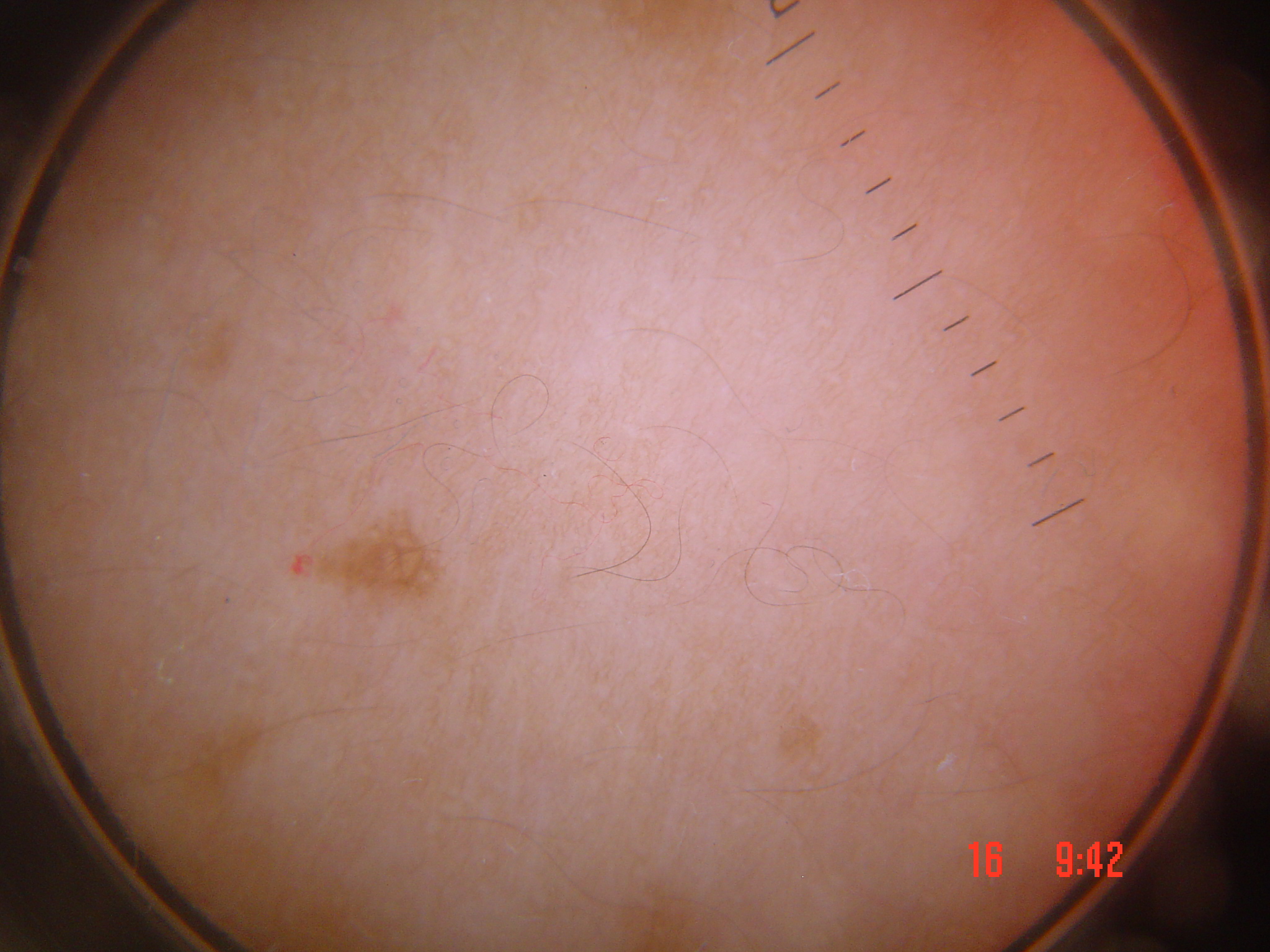  image: dermoscopy
  diagnosis:
    name: lentigo simplex
    code: ls
    malignancy: benign
    super_class: melanocytic
    confirmation: expert consensus